An image taken at a distance; the leg is involved.
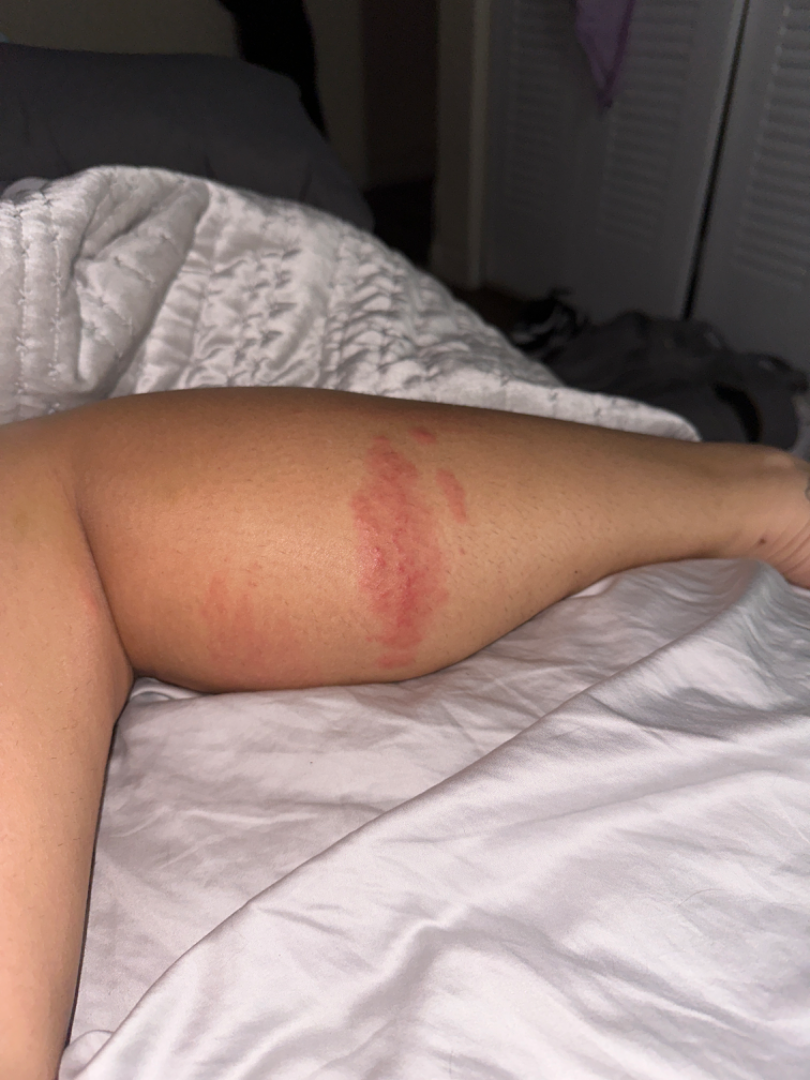The condition could not be reliably identified from the image.